A skin lesion imaged with a dermatoscope; a male subject aged 83 or older — 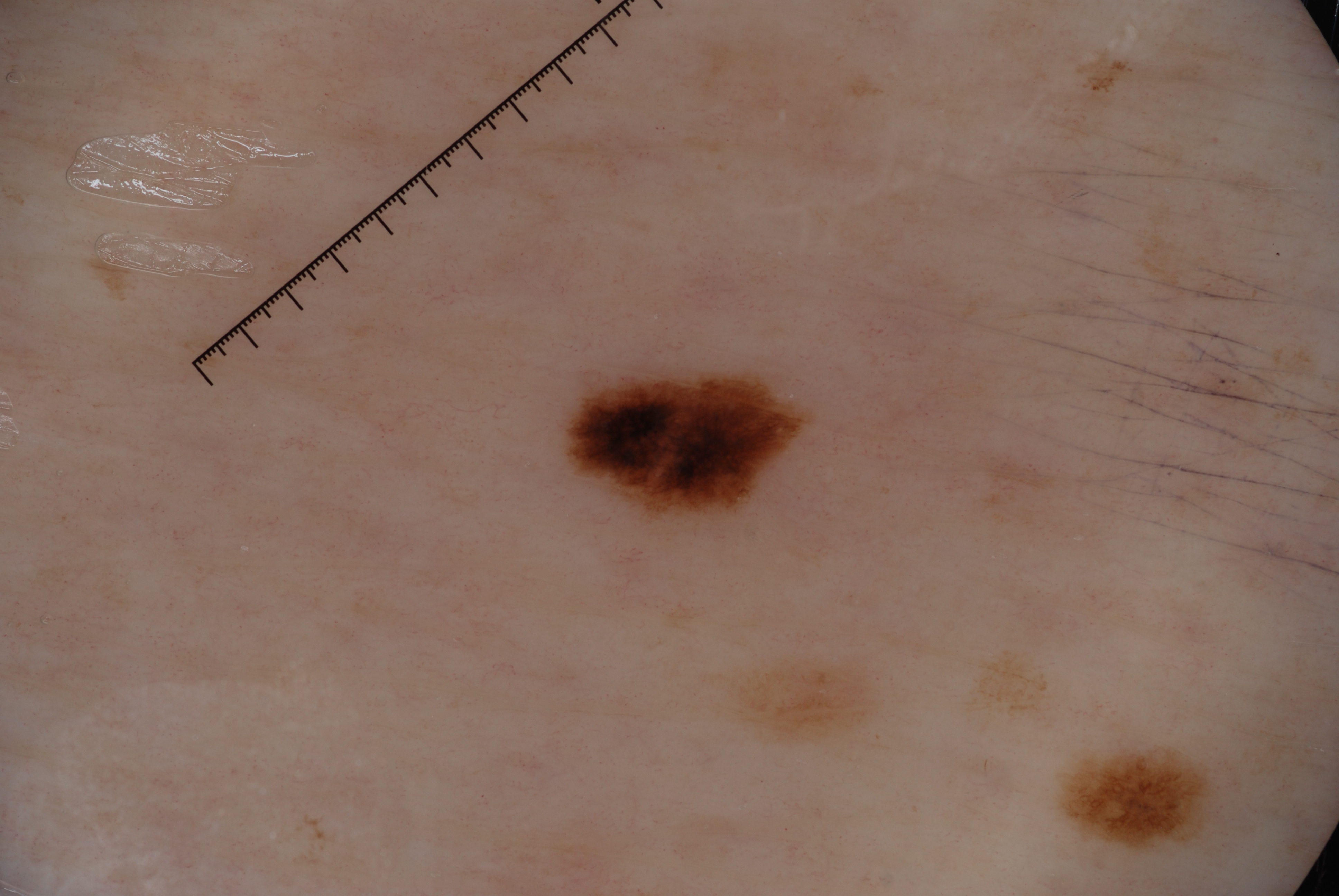lesion extent: small
lesion location: bbox=[555, 343, 830, 537]
dermoscopic pattern: pigment network
diagnosis: a melanocytic nevus, a benign skin lesion